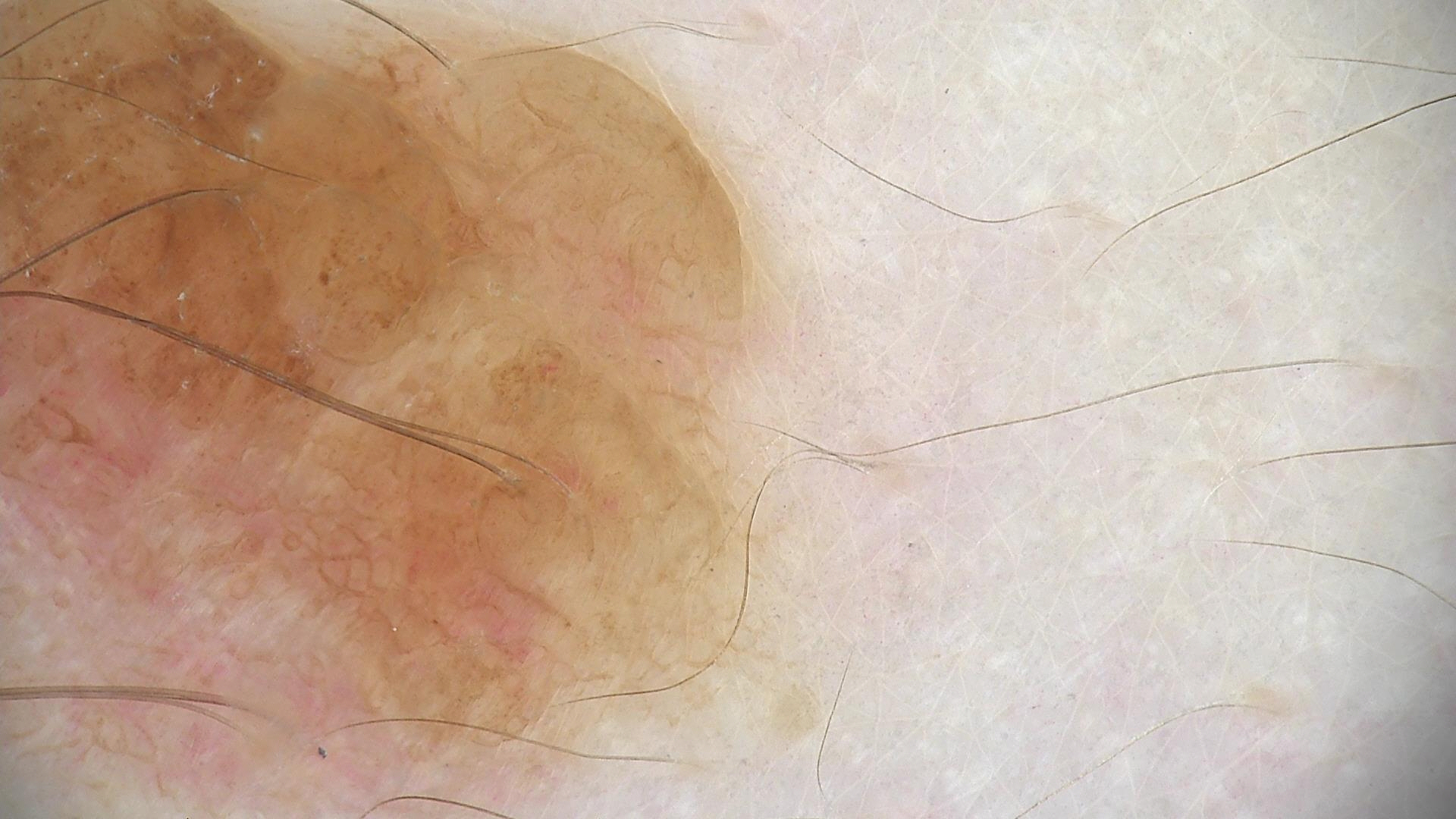Classified as a dermal nevus.